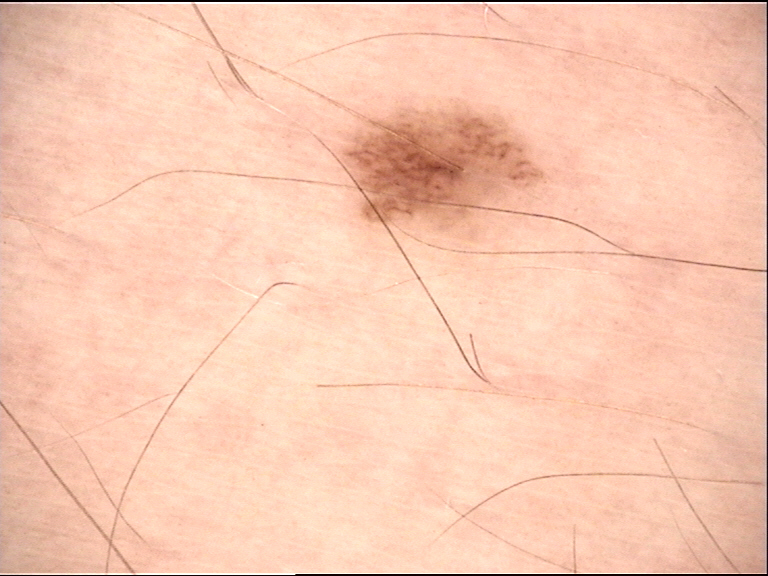Consistent with a junctional nevus.